A female subject 84 years of age; a dermoscopy image of a skin lesion; referred for assessment of suspected basal cell carcinoma; the patient describes having few moles overall.
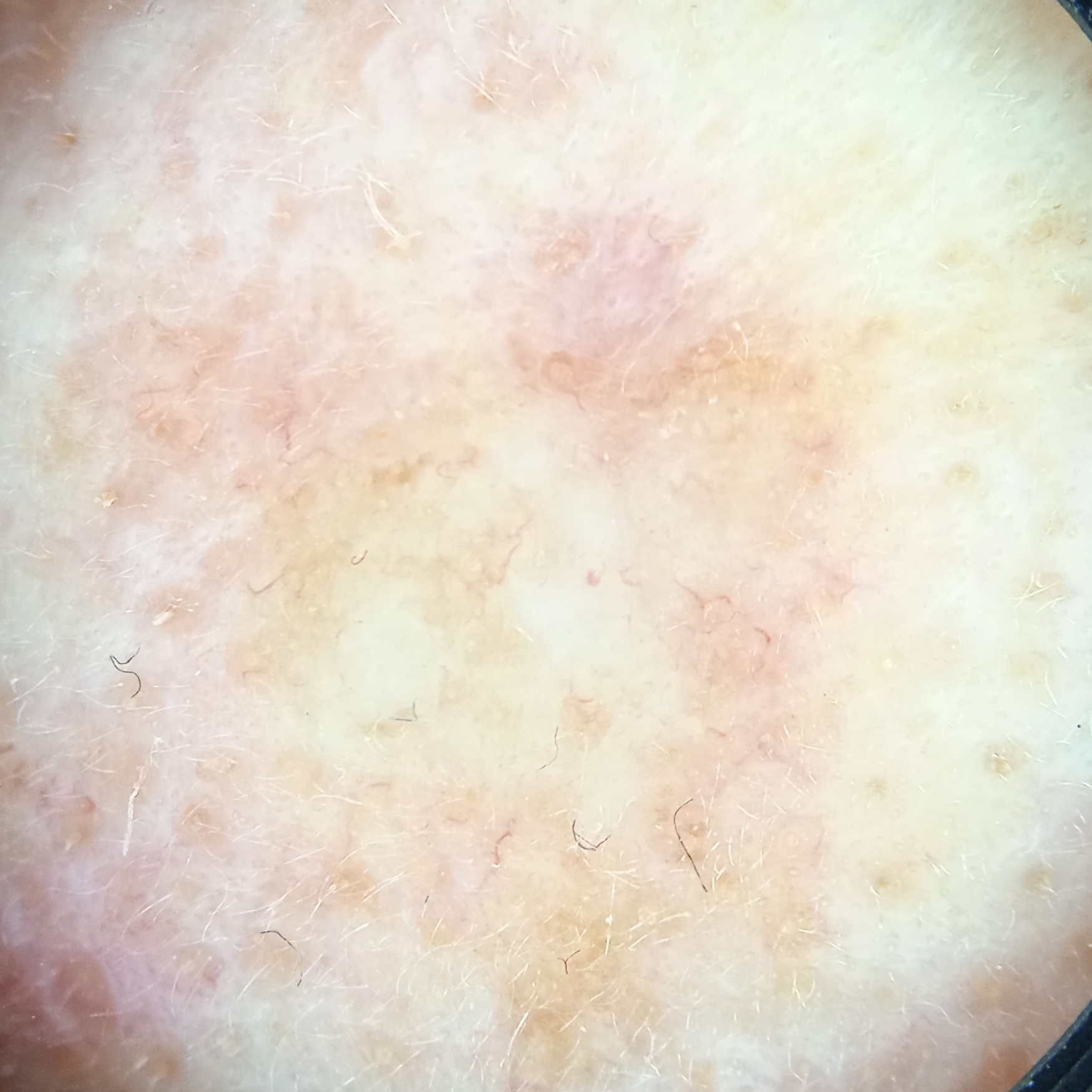Case:
– body site — the face
– diagnosis — basal cell carcinoma (biopsy-proven)